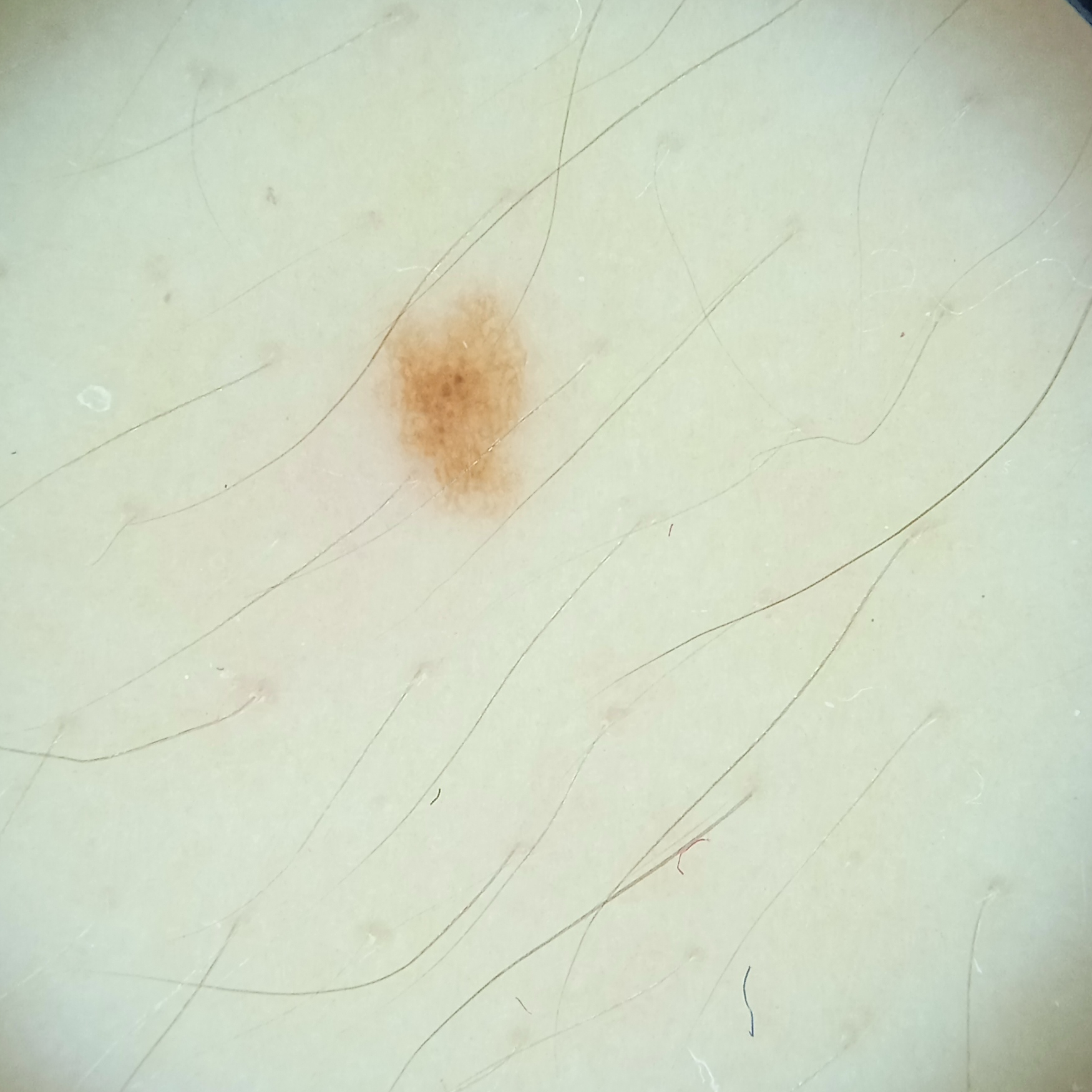Findings:
- sun reaction · skin reddens with sun exposure
- patient · female, aged 20
- body site · an arm
- diameter · 2.5 mm
- diagnosis · melanocytic nevus (dermatologist consensus)